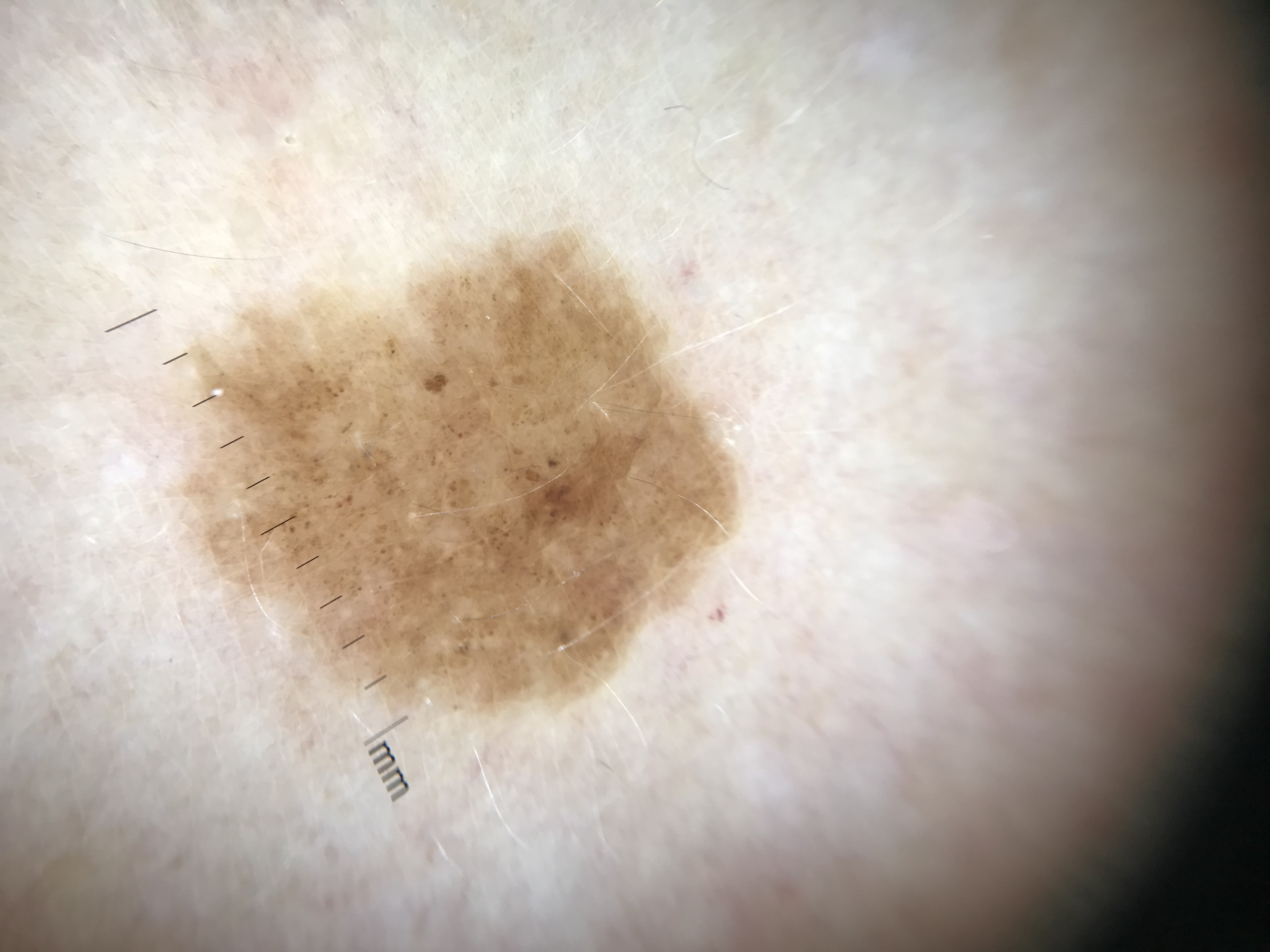Findings: A dermoscopy image of a single skin lesion. Impression: Diagnosed as a dysplastic junctional nevus.